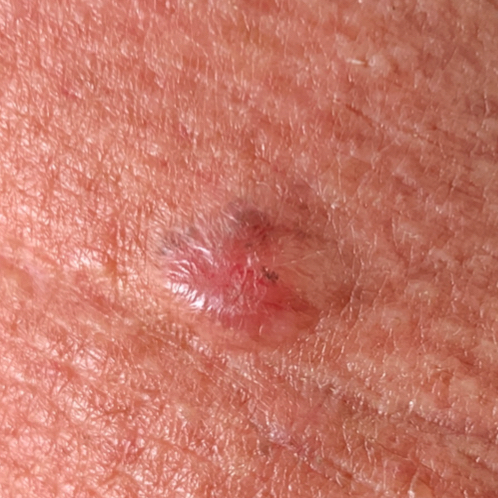A clinical close-up photograph of a skin lesion. A male subject 55 years of age. The lesion involves the neck. The patient reports that the lesion is elevated, but has not bled and does not itch. Histopathological examination showed a basal cell carcinoma.